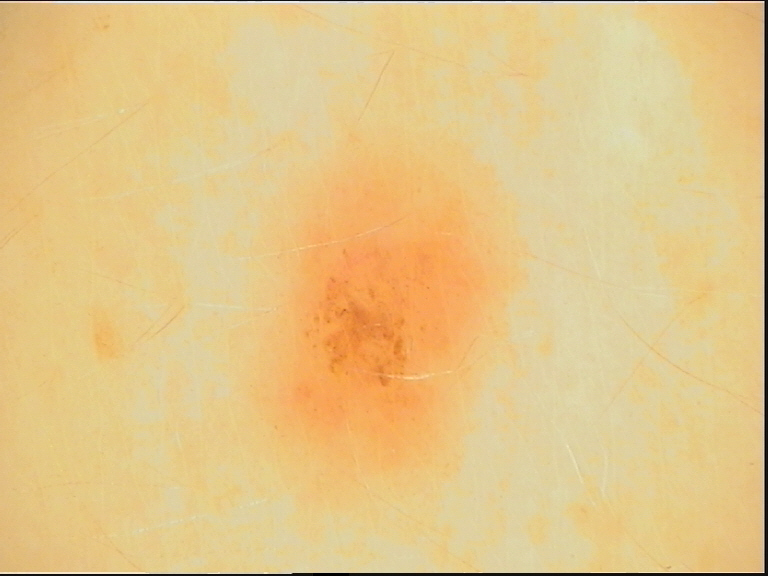A dermoscopy image of a single skin lesion. Consistent with a dysplastic junctional nevus.